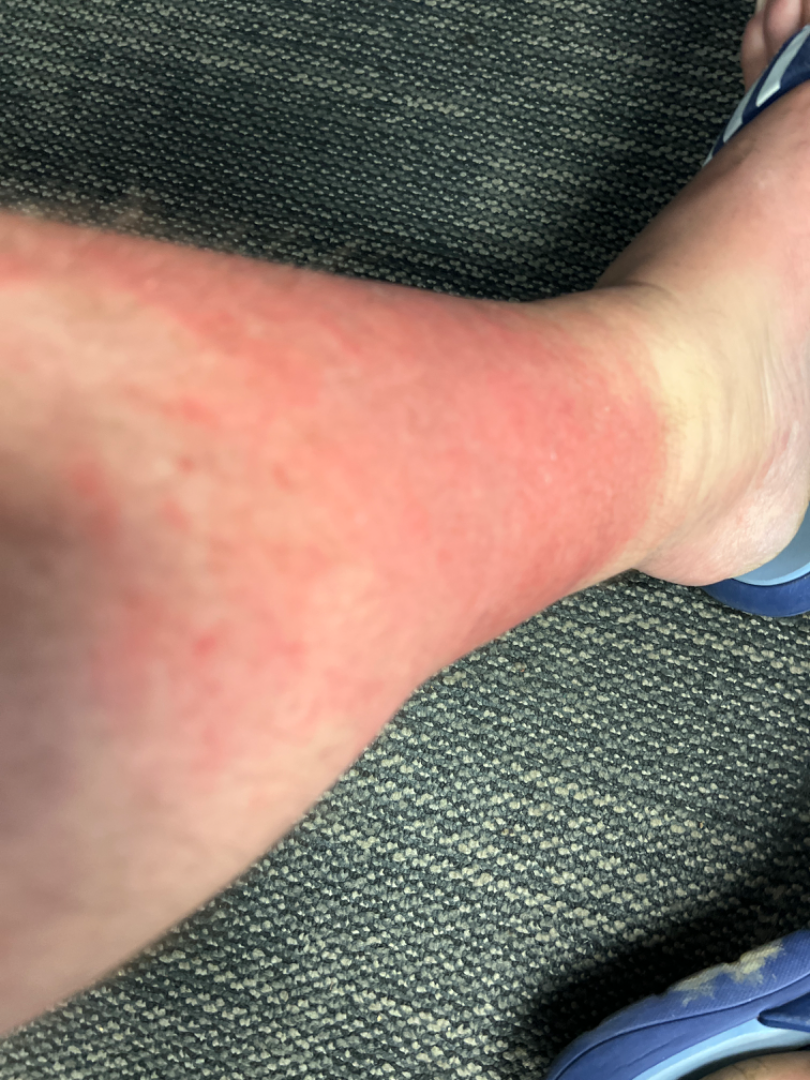No differential diagnosis could be assigned on photographic review. The lesion involves the leg. Male contributor, age 30–39. Associated systemic symptoms include joint pain and fatigue. The patient described the issue as a rash. An image taken at an angle. The lesion is associated with enlargement, burning, bothersome appearance and pain. Texture is reported as rough or flaky and flat.